The photograph is a close-up of the affected area — 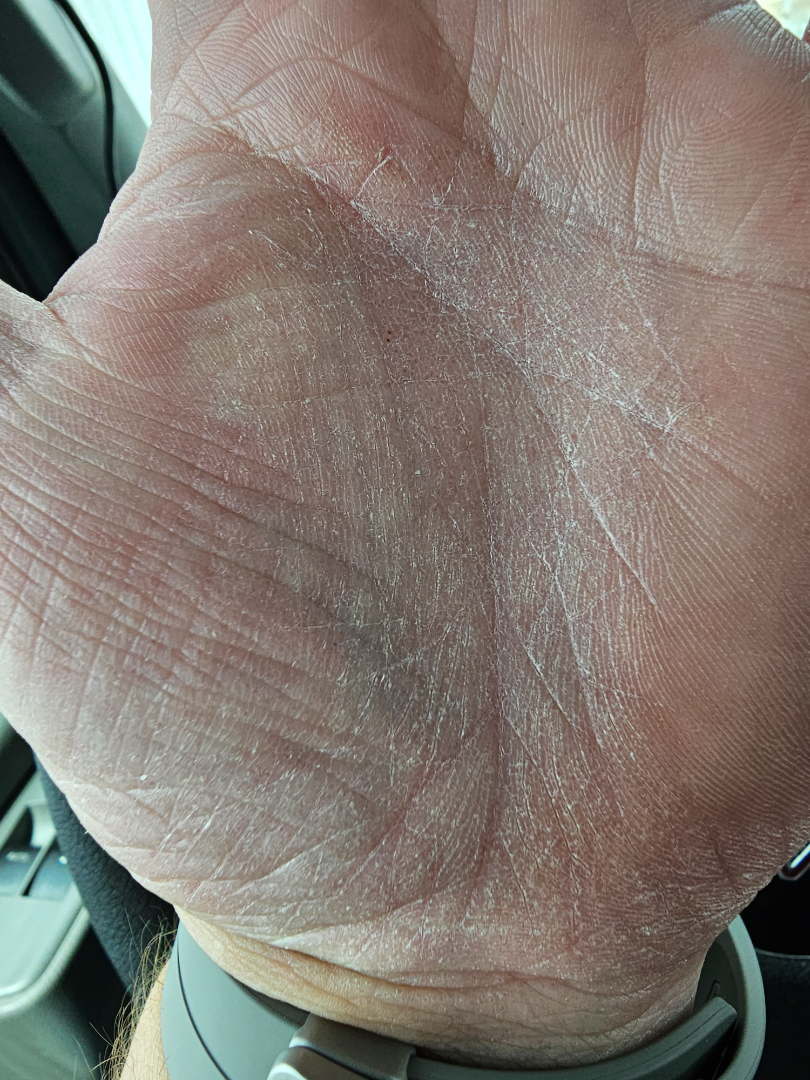The patient considered this a rash. The contributor notes the condition has been present for more than one year. Texture is reported as rough or flaky. The contributor notes itching. No relevant systemic symptoms. A single dermatologist reviewed the case: the impression was split between Tinea, Eczema and Irritant Contact Dermatitis.